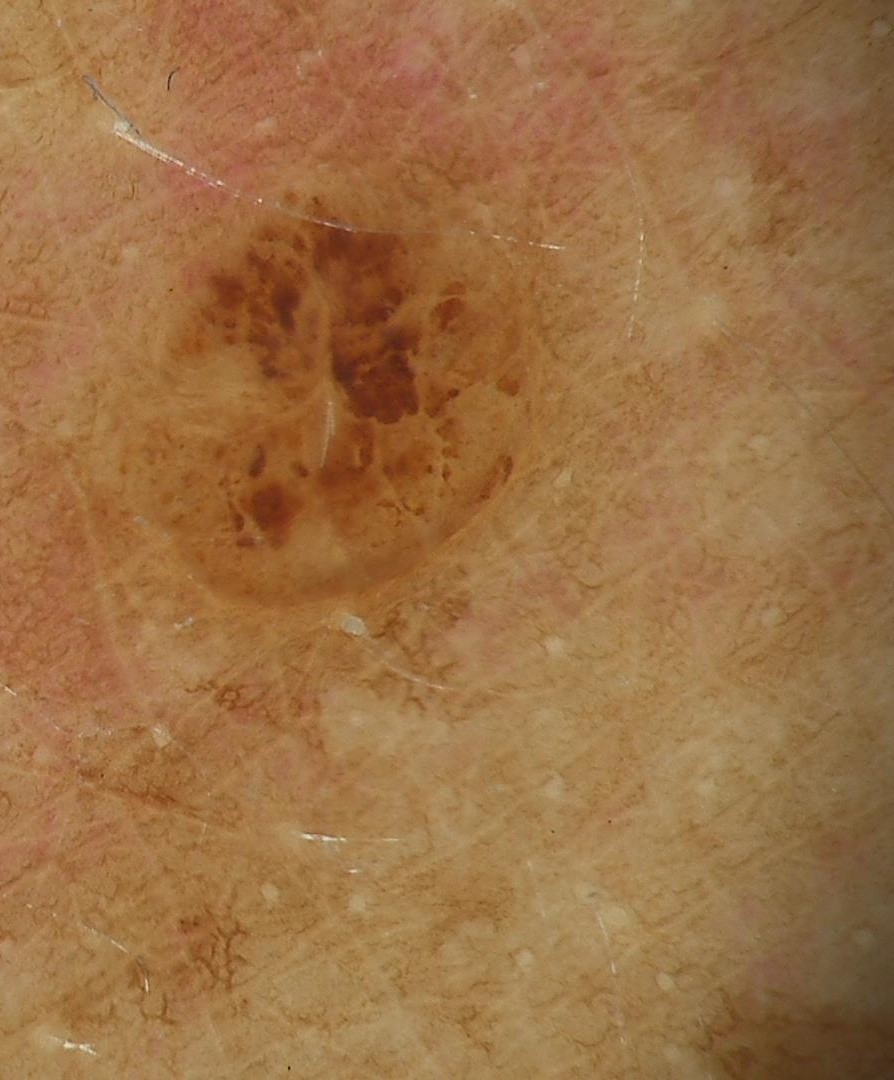A dermoscopic photograph of a skin lesion. Consistent with a banal lesion — a dermal nevus.